The chart notes pesticide exposure · a male patient aged 70 · skin type II · a smartphone photograph of a skin lesion.
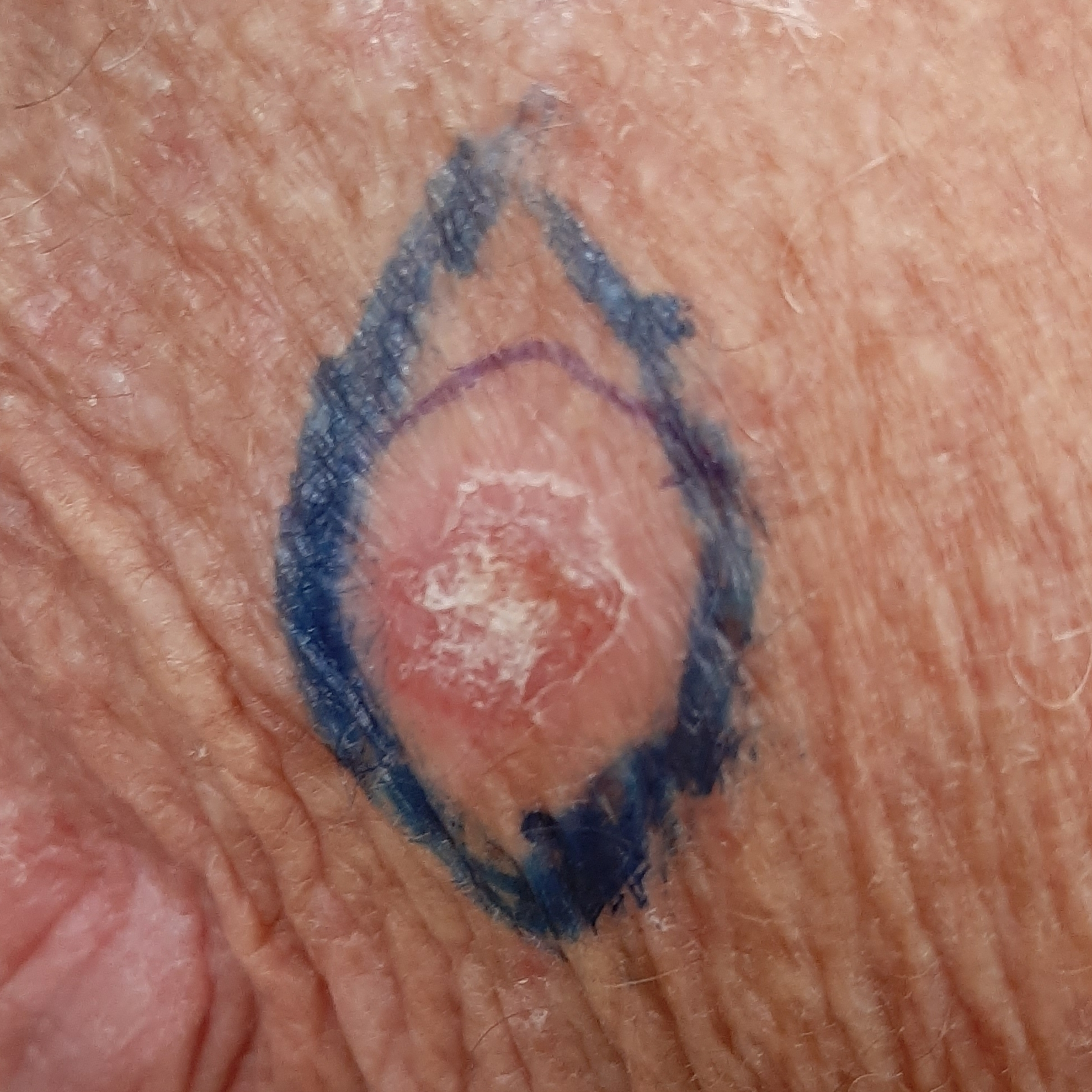• site · a forearm
• lesion size · approx. 19 × 15 mm
• reported symptoms · elevation, itching
• diagnosis · basal cell carcinoma (biopsy-proven)